Dermoscopy of a skin lesion:
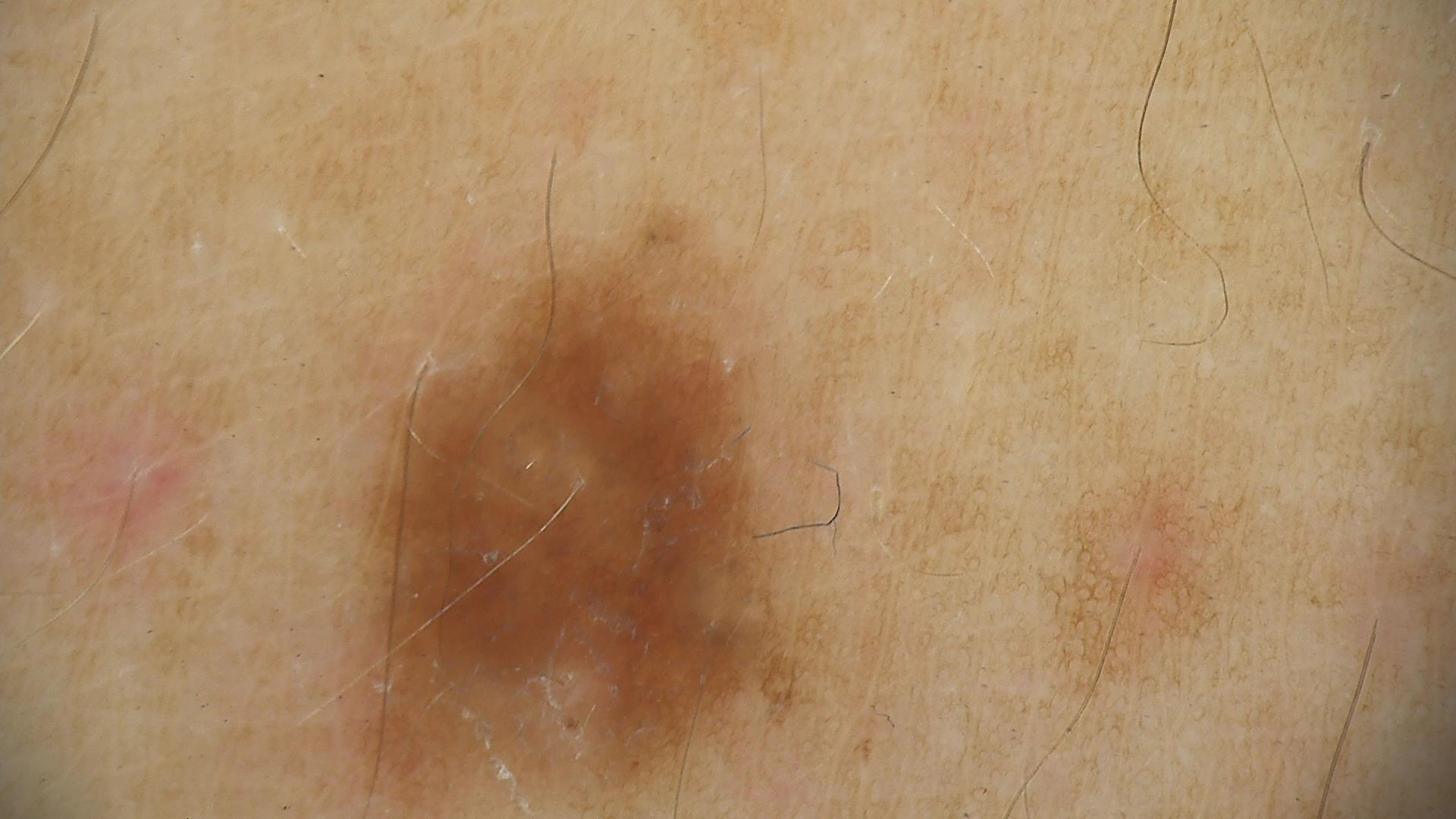Consistent with a dysplastic junctional nevus.